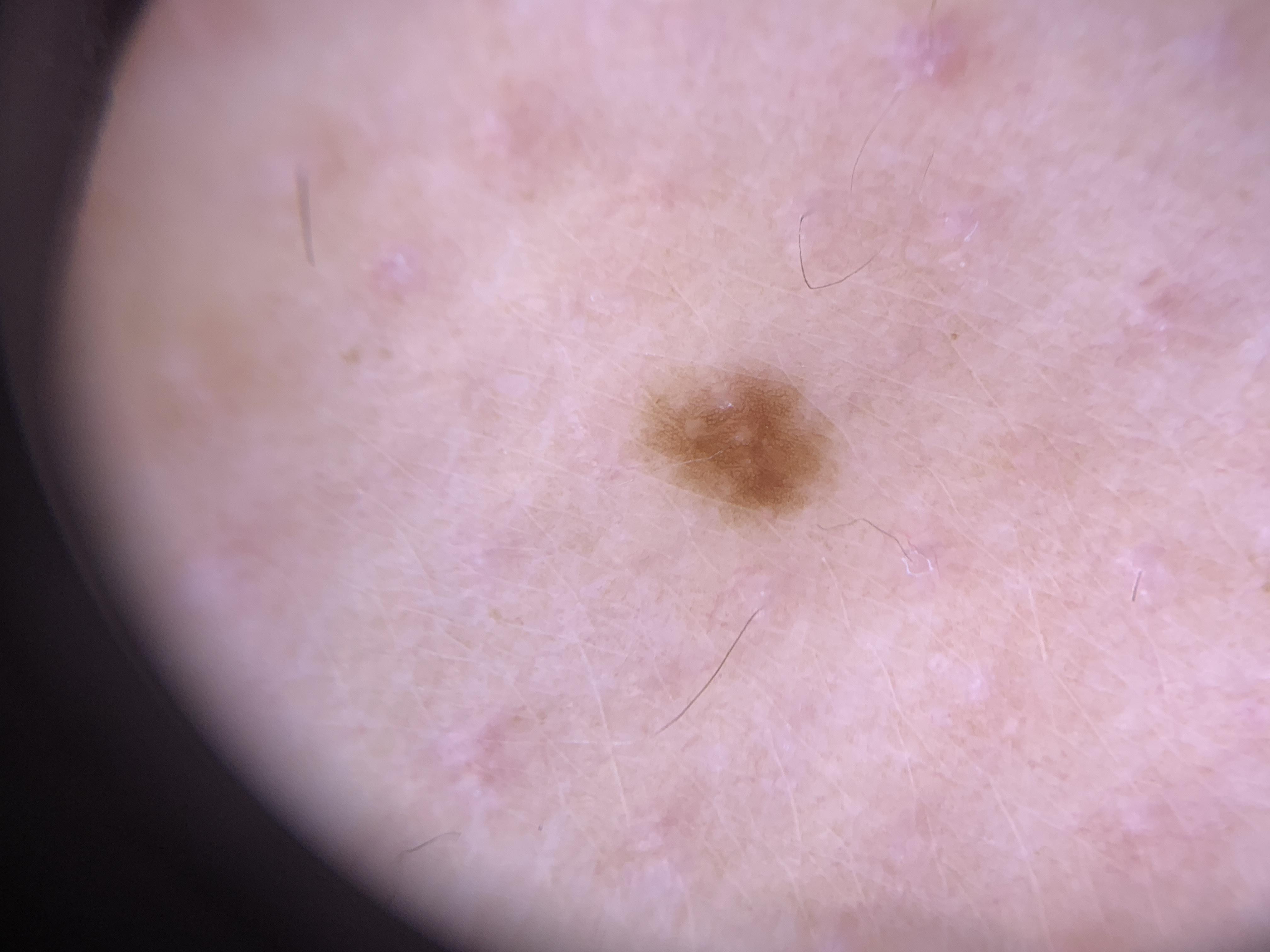Dermoscopy of a skin lesion. Recorded as Fitzpatrick I. A female subject about 25 years old. The lesion involves an upper extremity. The clinical impression was a nevus.